Texture is reported as raised or bumpy · the contributor is female · the photo was captured at an angle · the patient reports itching · the affected area is the arm: 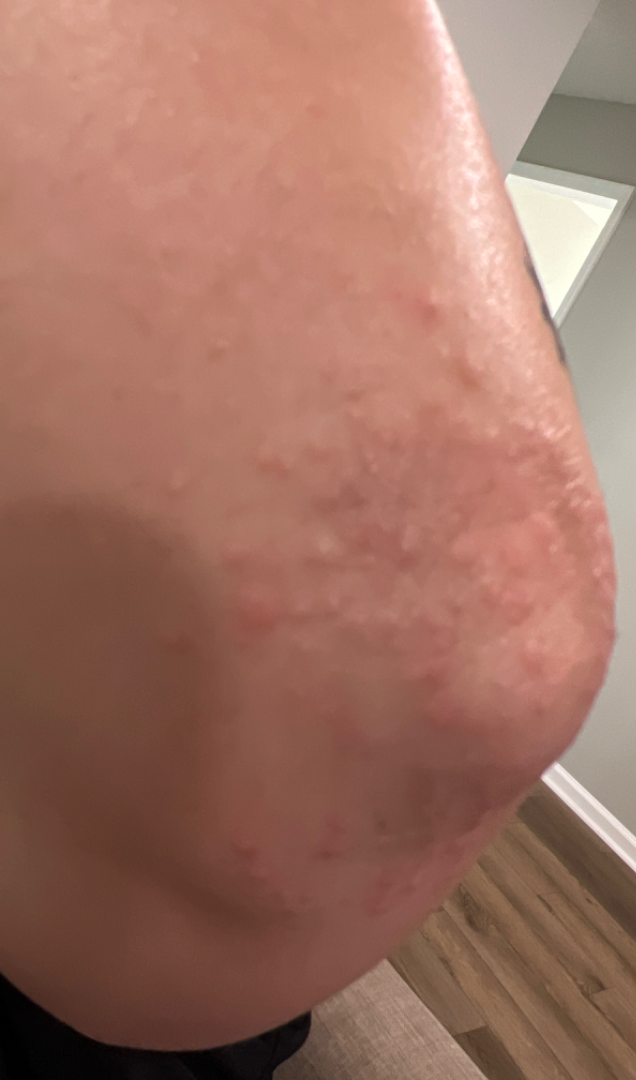Assessment:
On remote review of the image, the impression was split between Eczema and Lichen Simplex Chronicus; less probable is Psoriasis; less likely is Perforating dermatosis; a more distant consideration is Granuloma annulare; a remote consideration is Dermatitis herpetiformis.